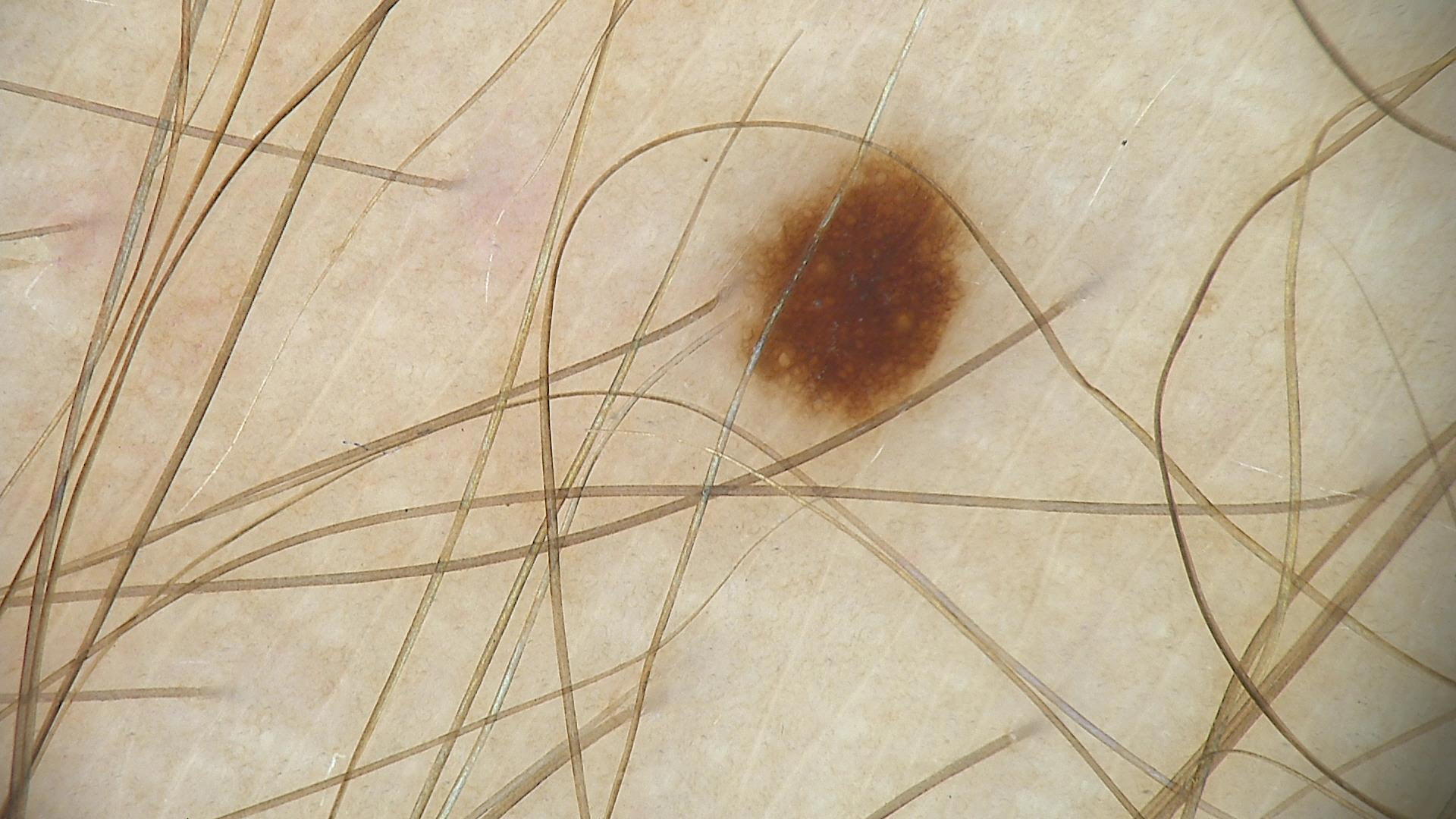diagnosis: dysplastic junctional nevus (expert consensus)